A dermoscopic image of a skin lesion · the patient is FST I · a male patient aged around 85 or older:
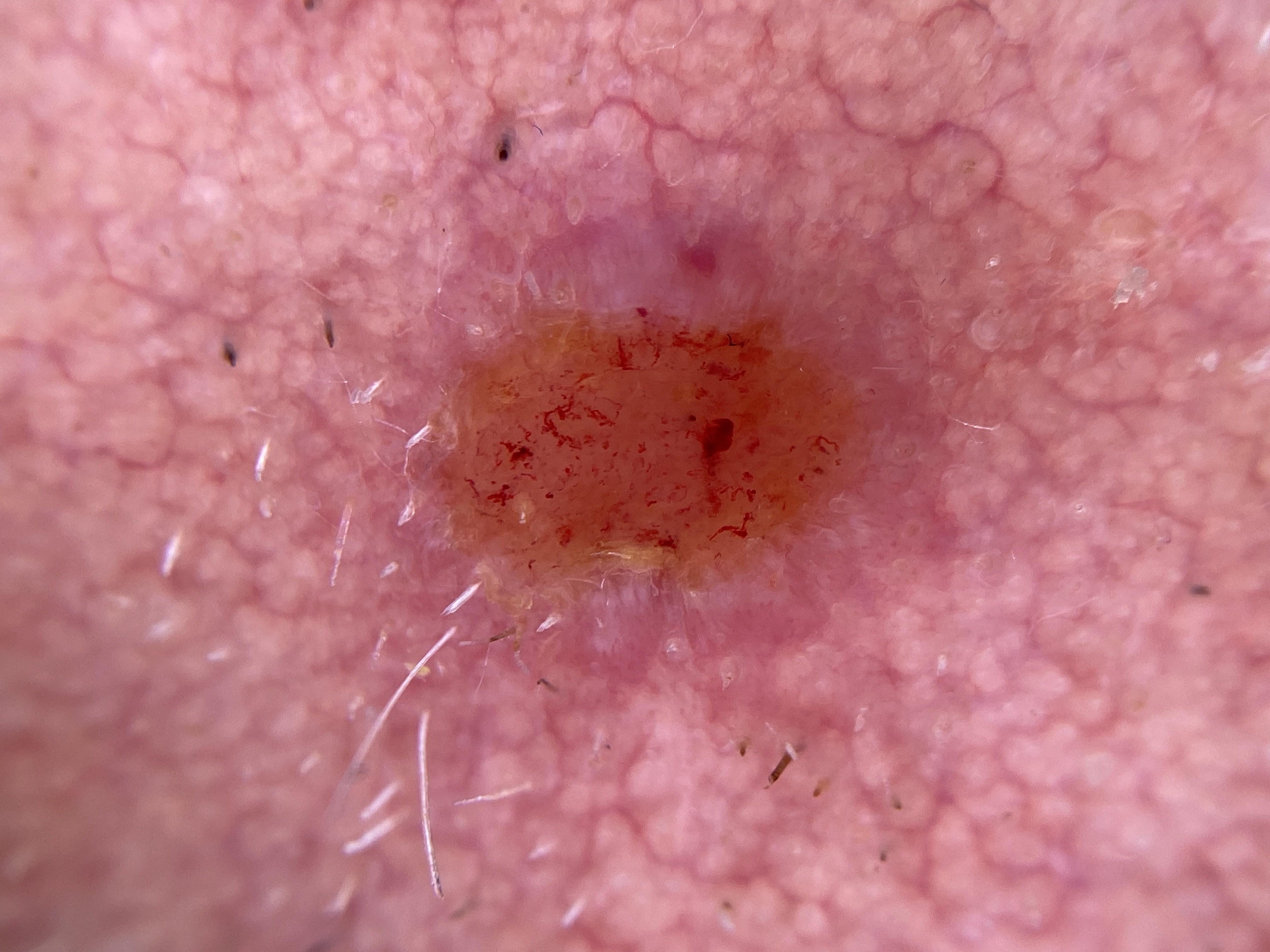{
  "diagnosis": {
    "name": "Basal cell carcinoma",
    "malignancy": "malignant",
    "confirmation": "histopathology",
    "lineage": "adnexal"
  }
}